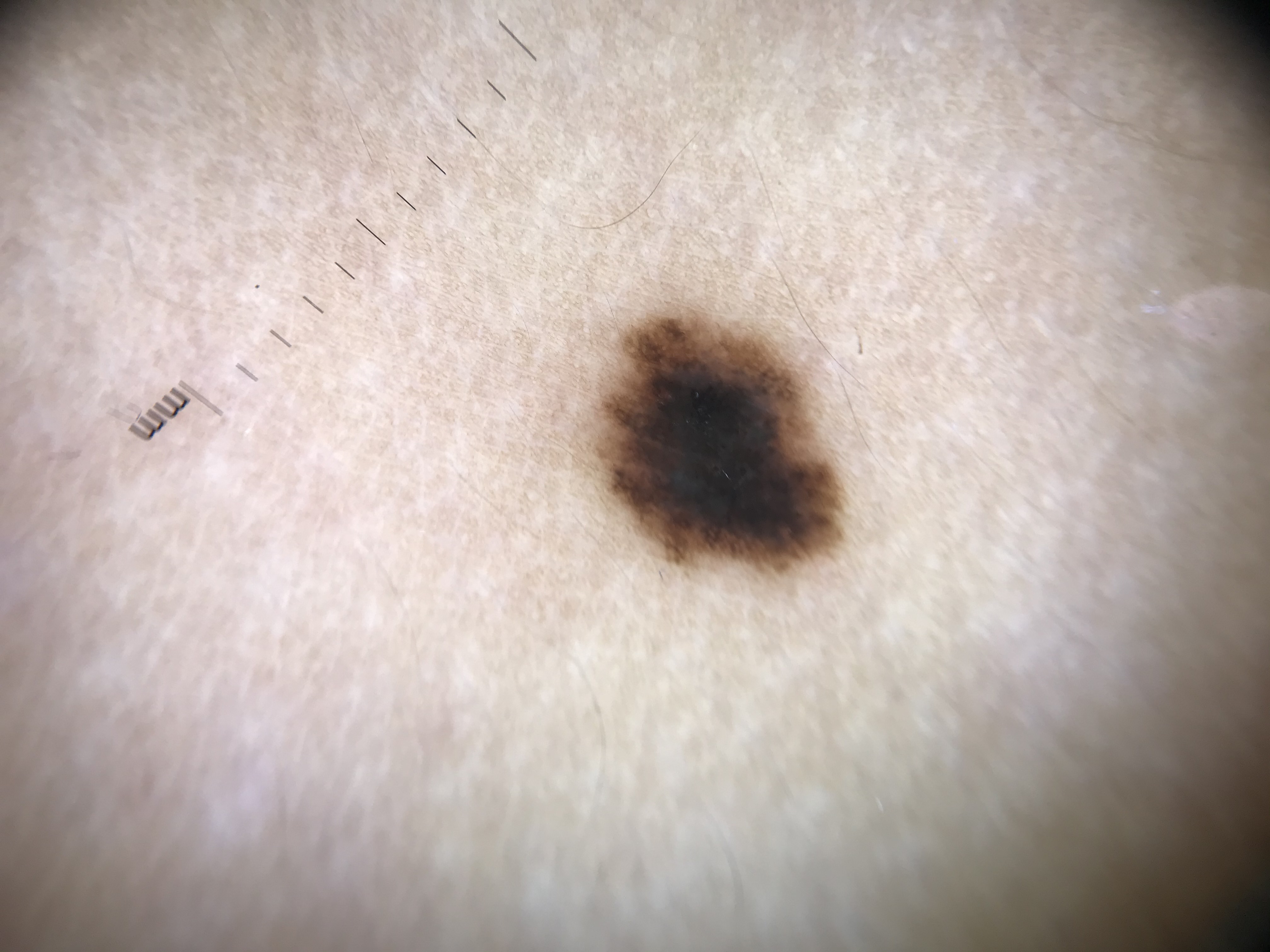A dermoscopic close-up of a skin lesion. Diagnosed as a dysplastic junctional nevus.